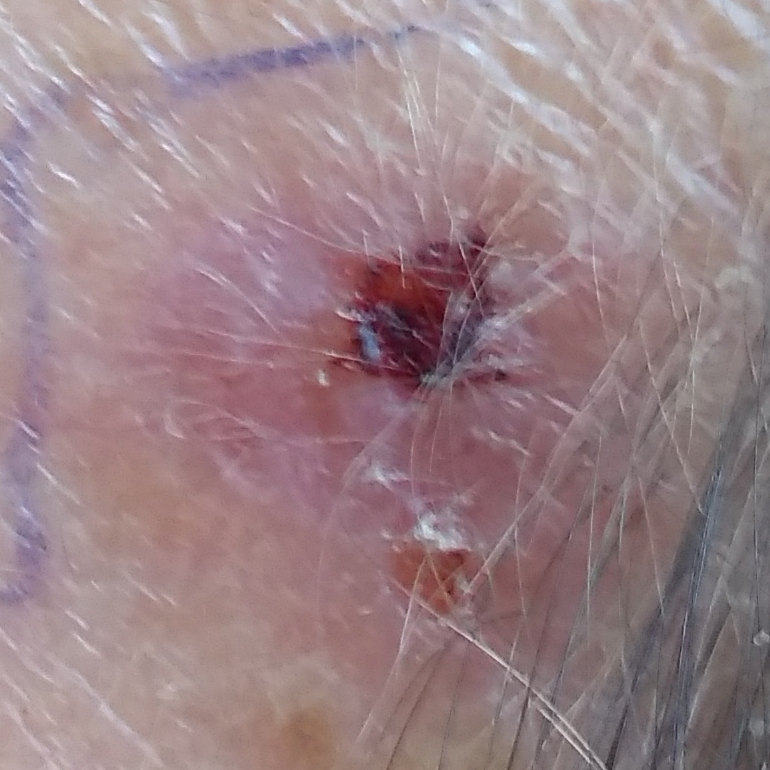Q: Patient demographics?
A: female, in their late 50s
Q: How was this image acquired?
A: clinical photograph
Q: What symptoms does the patient report?
A: growth, elevation, bleeding, change in appearance
Q: What is the diagnosis?
A: basal cell carcinoma (biopsy-proven)